A dermoscopy image of a single skin lesion.
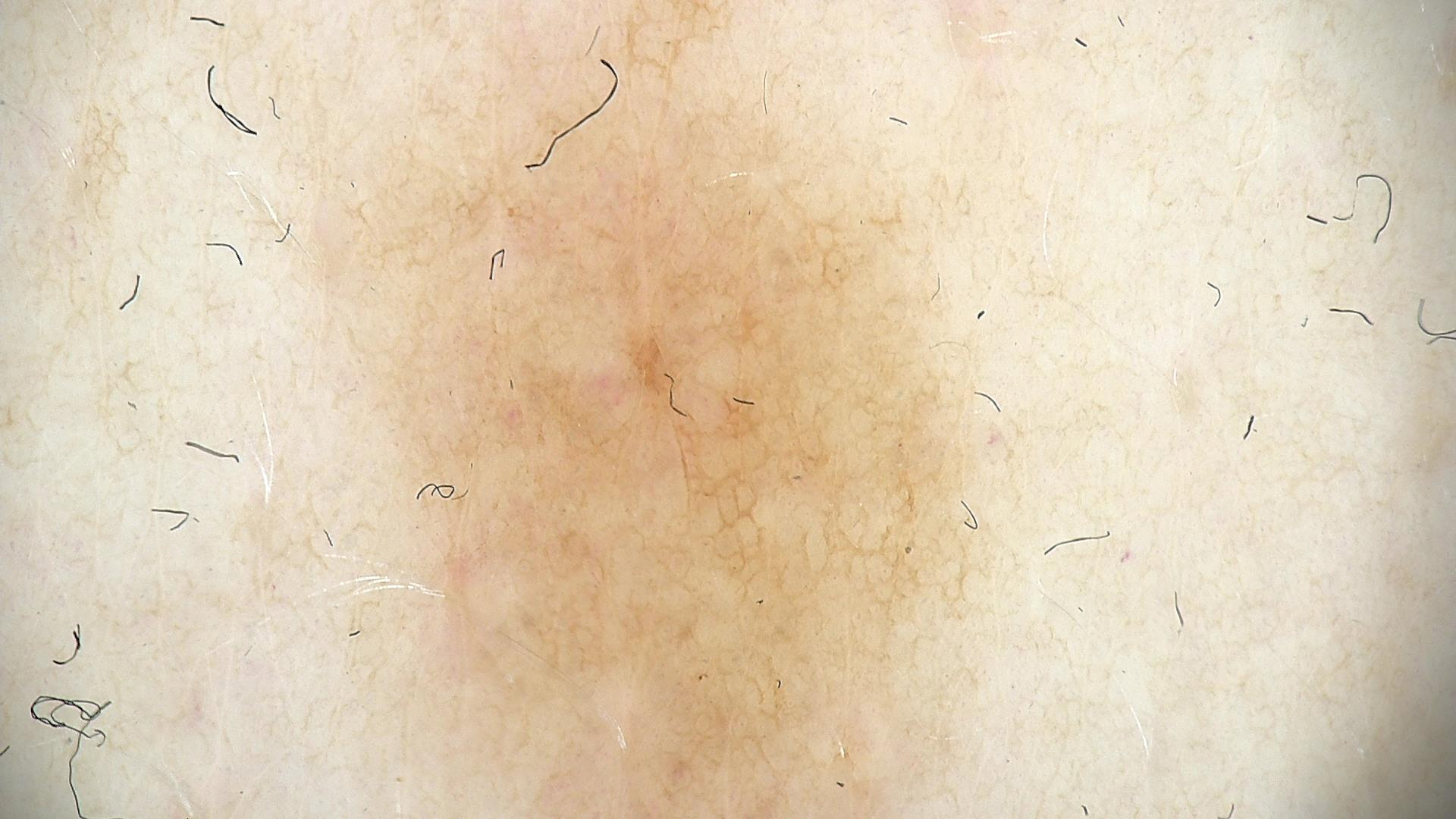{
  "diagnosis": {
    "name": "junctional nevus",
    "code": "jb",
    "malignancy": "benign",
    "super_class": "melanocytic",
    "confirmation": "expert consensus"
  }
}